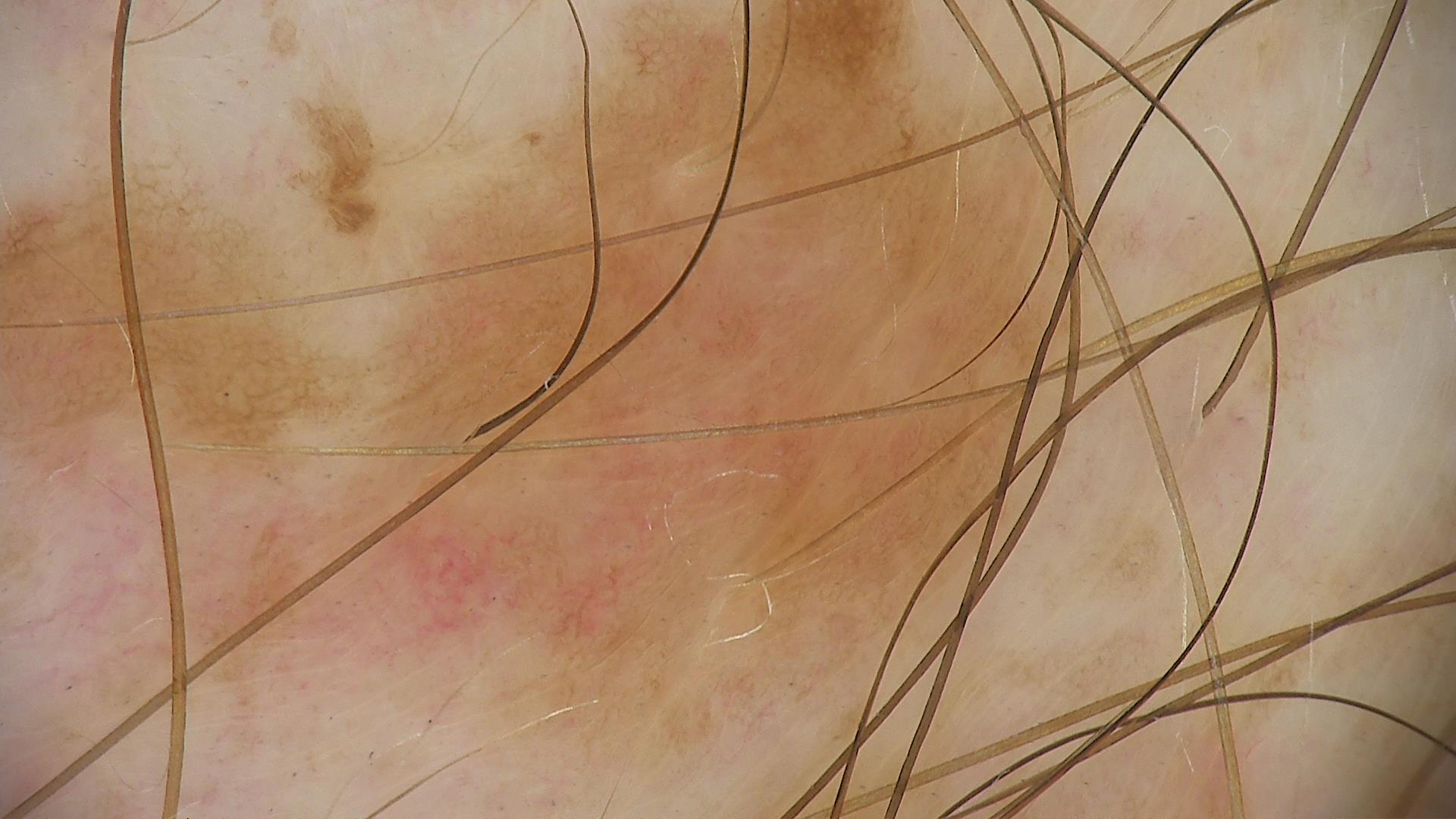A dermoscopy image of a single skin lesion. Classified as a banal lesion — a compound nevus.